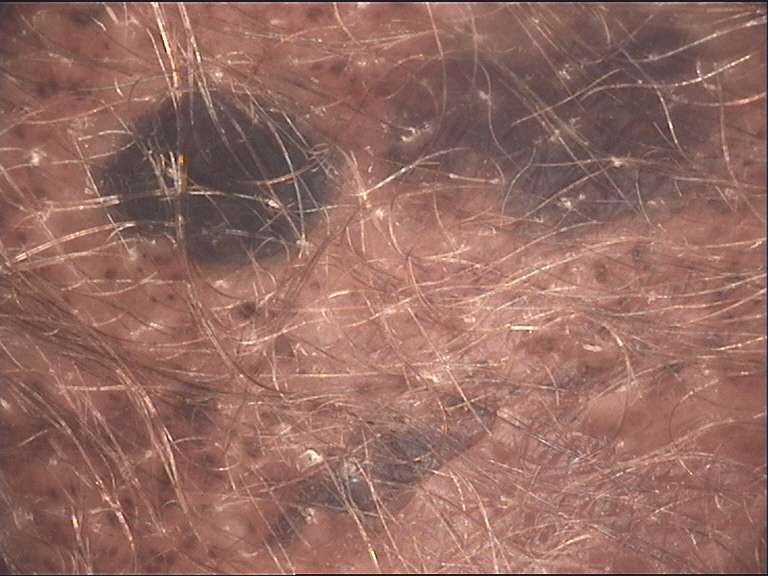A dermoscopy image of a single skin lesion.
The diagnosis was a banal lesion — a congenital compound nevus.